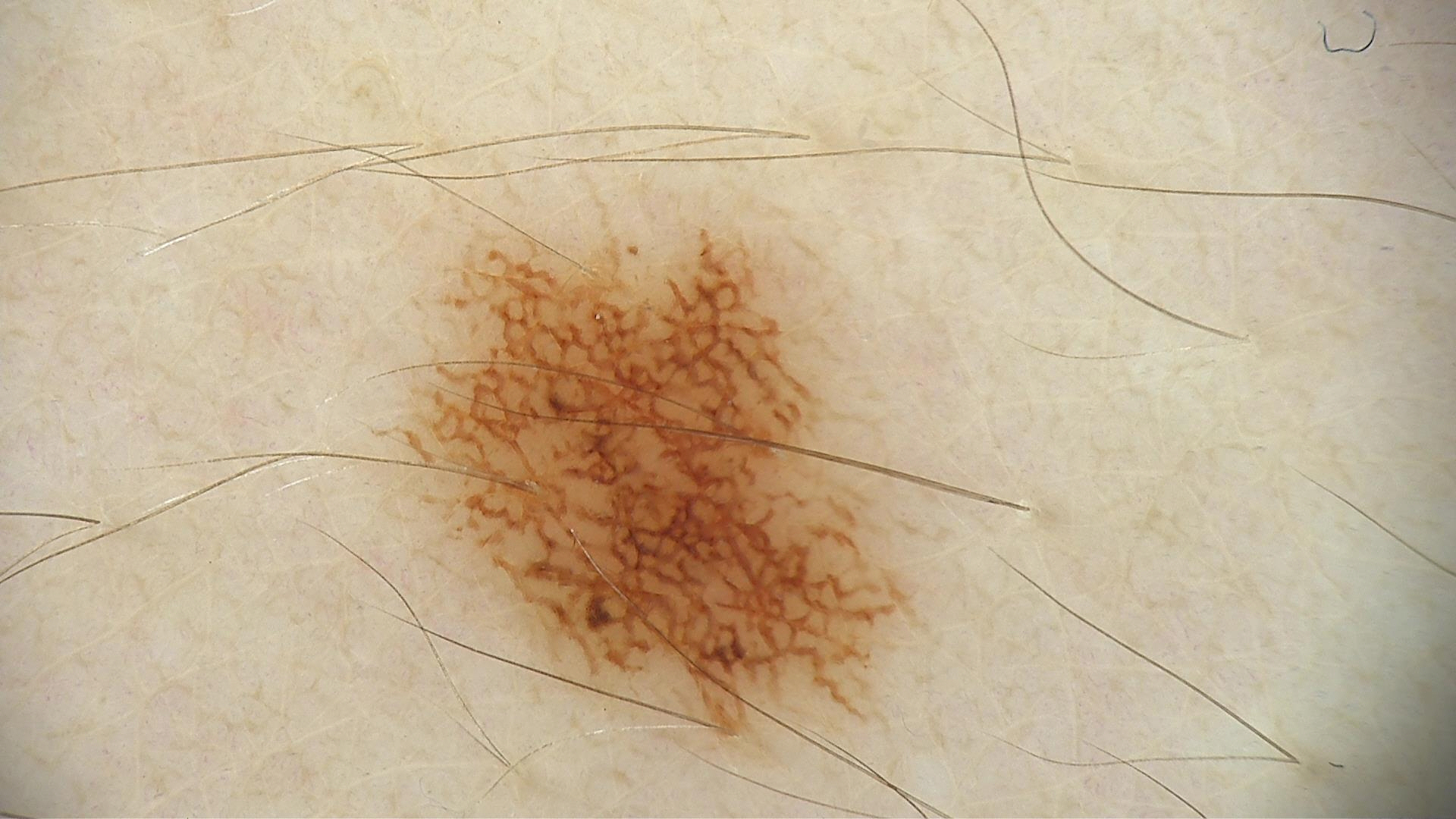Diagnosed as a dysplastic junctional nevus.